A dermoscopy image of a single skin lesion:
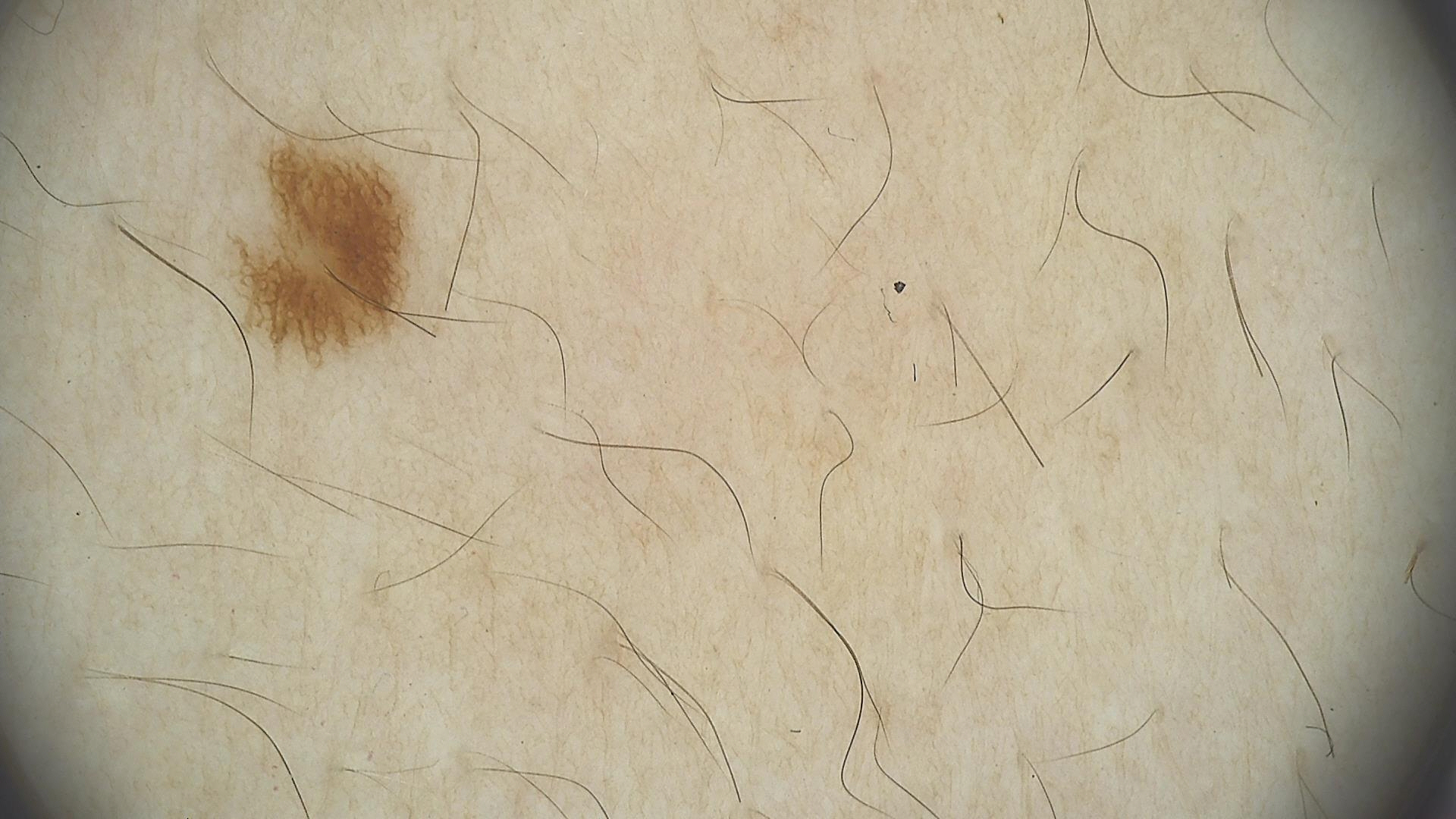Q: What is the lesion category?
A: banal
Q: What was the diagnostic impression?
A: junctional nevus (expert consensus)